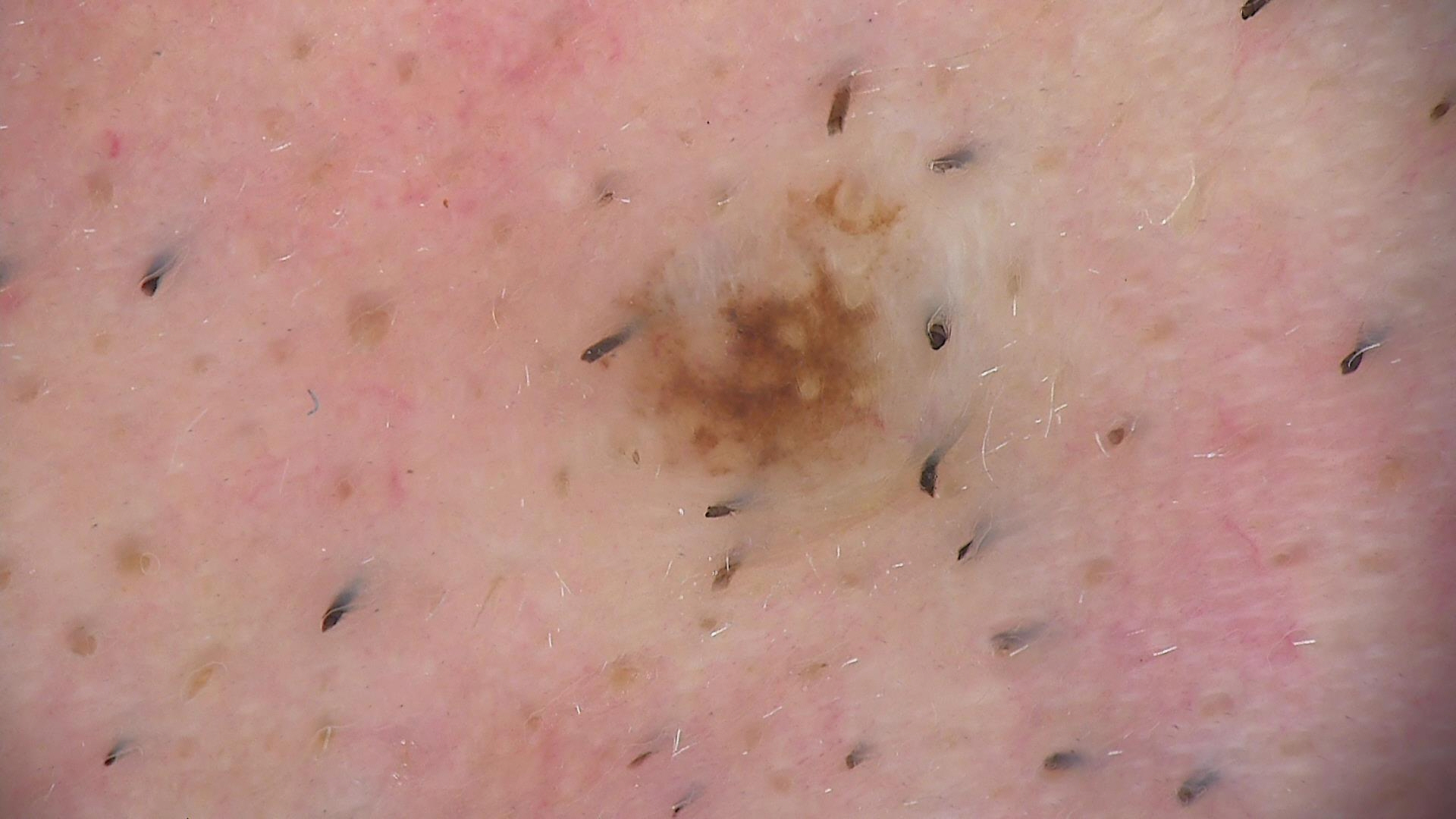Diagnosed as a compound nevus.